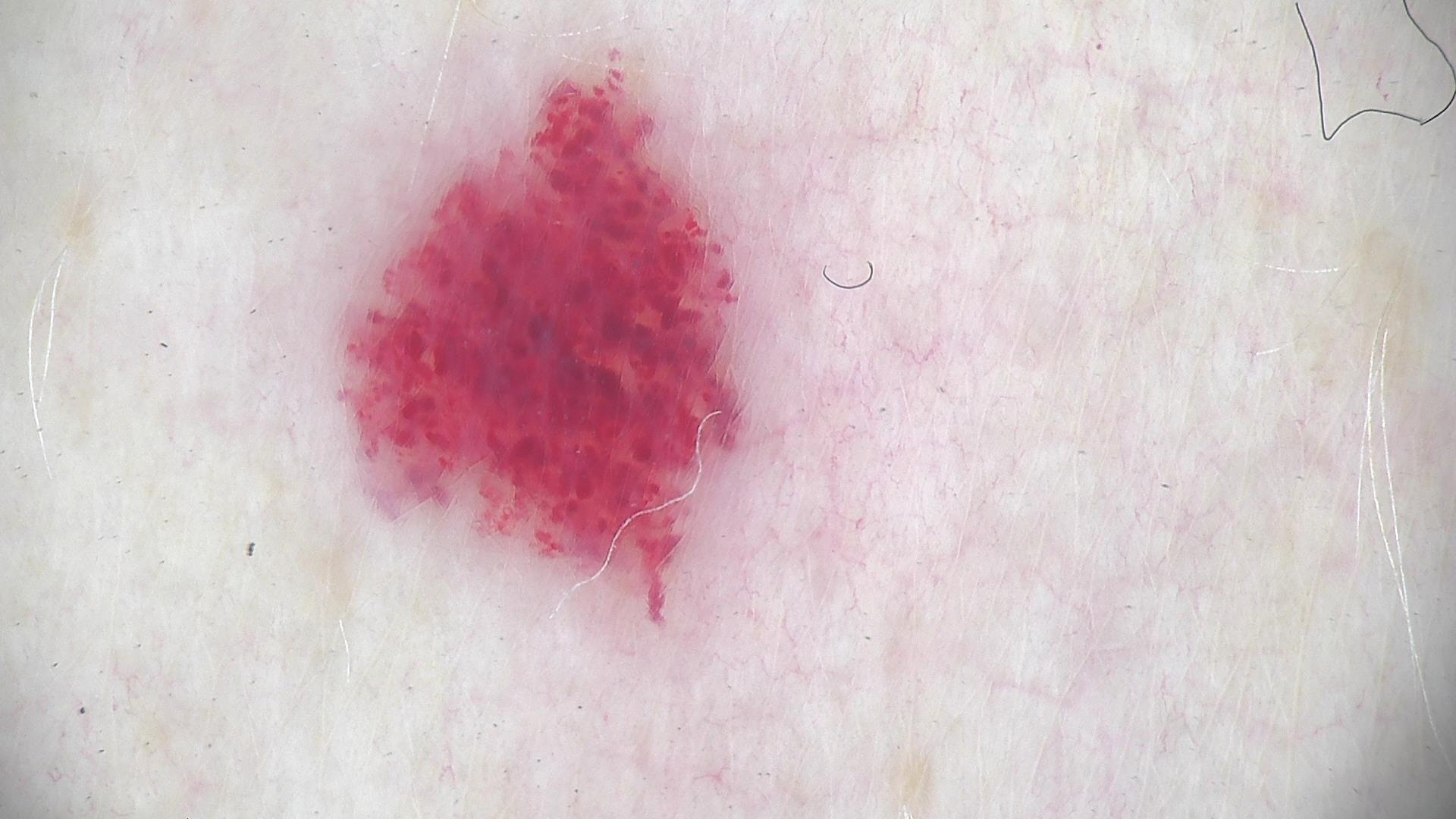The diagnostic label was a hemangioma.